A wide-field clinical photograph of a skin lesion; a male patient approximately 55 years of age; recorded as skin type II — 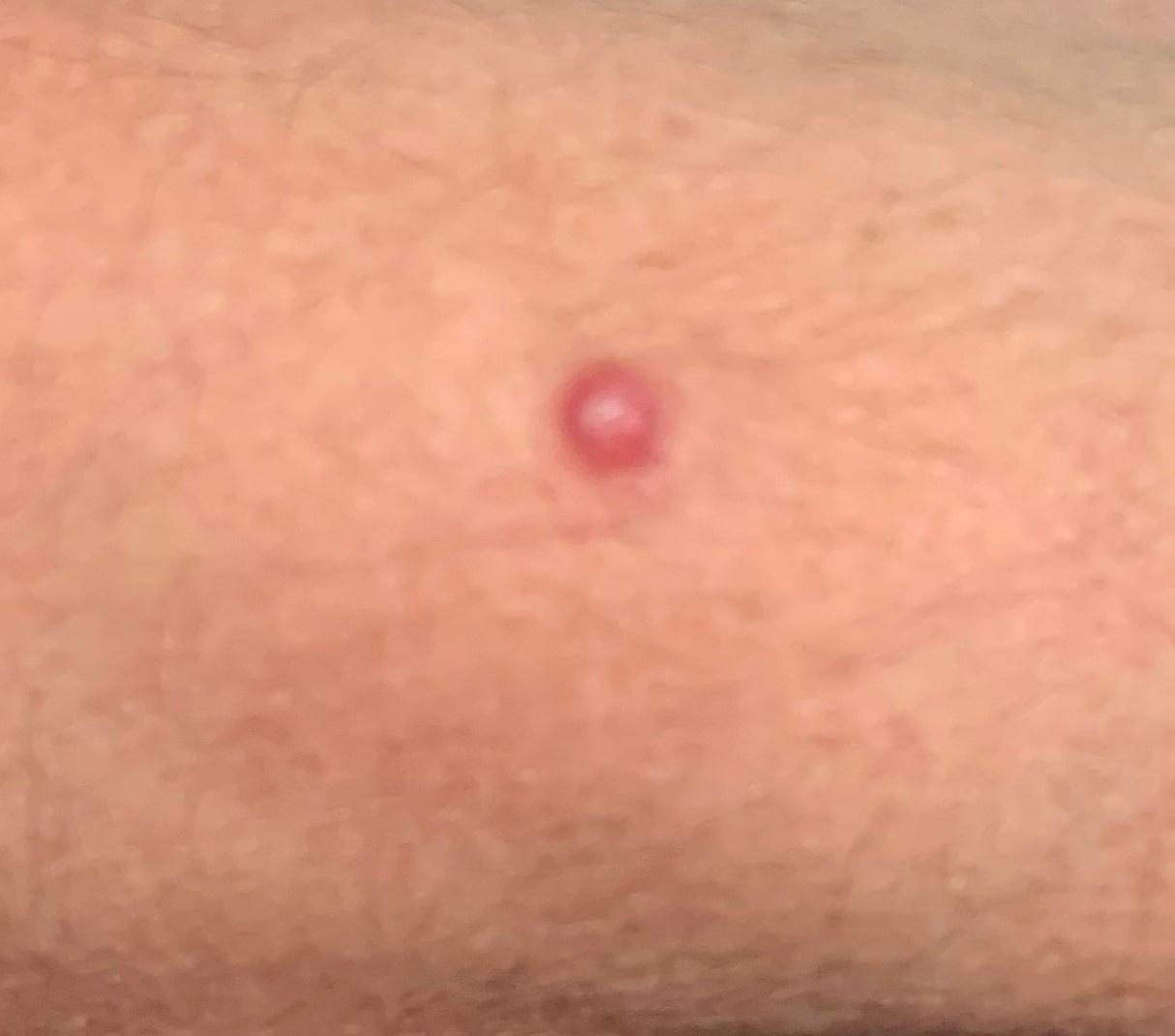body site: an upper extremity
pathology: Basal cell carcinoma (biopsy-proven)